Skin tone: lay reviewers estimated a Monk Skin Tone of 3, this is a close-up image.
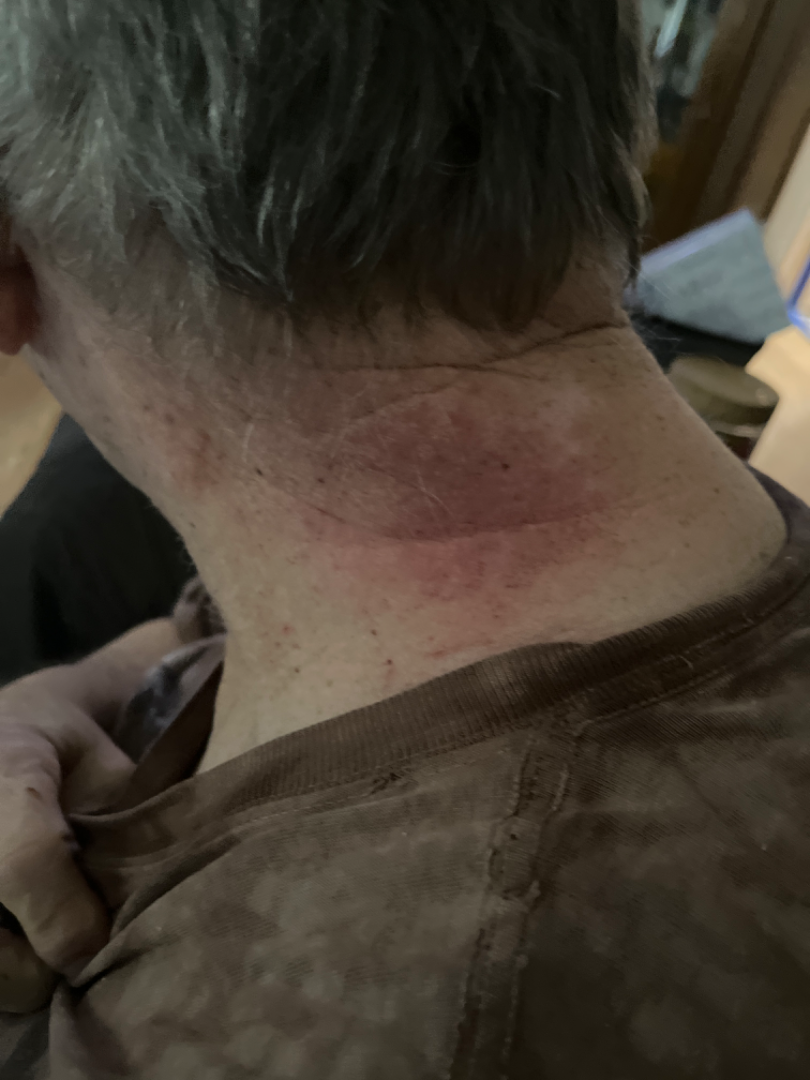Impression:
The case was difficult to assess from the available photograph.